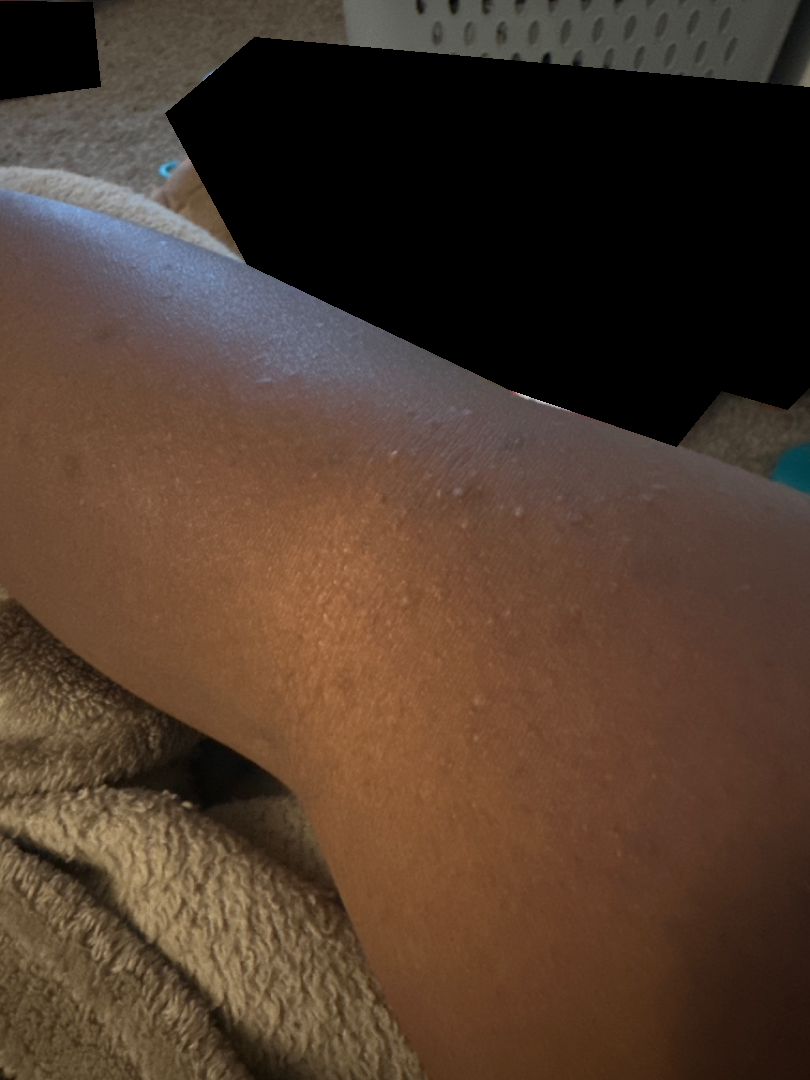shot type = at a distance
symptoms = bothersome appearance, enlargement, itching and burning
symptom duration = one to four weeks
contributor = female, age 18–29
constitutional symptoms = none reported
affected area = arm
self-categorized as = a rash
described texture = fluid-filled
assessment = Eczema (35%); Lichen nitidus (35%); Milia (15%); Hypersensitivity (15%)